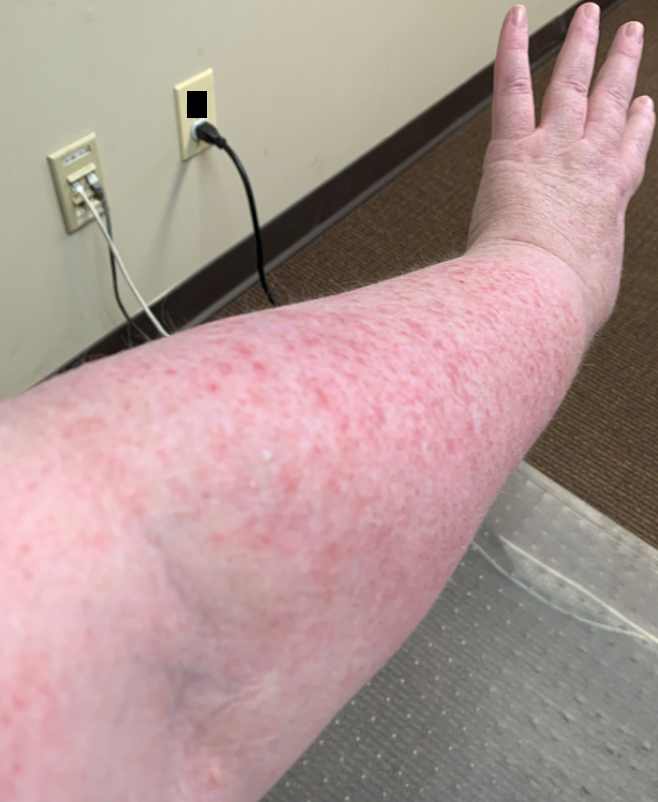anatomic site — head or neck and arm
image framing — close-up
patient — female, age 50–59
diagnostic considerations — most consistent with Drug Rash; also on the differential is Photodermatitis; also consider Eczema; less probable is Contact dermatitis